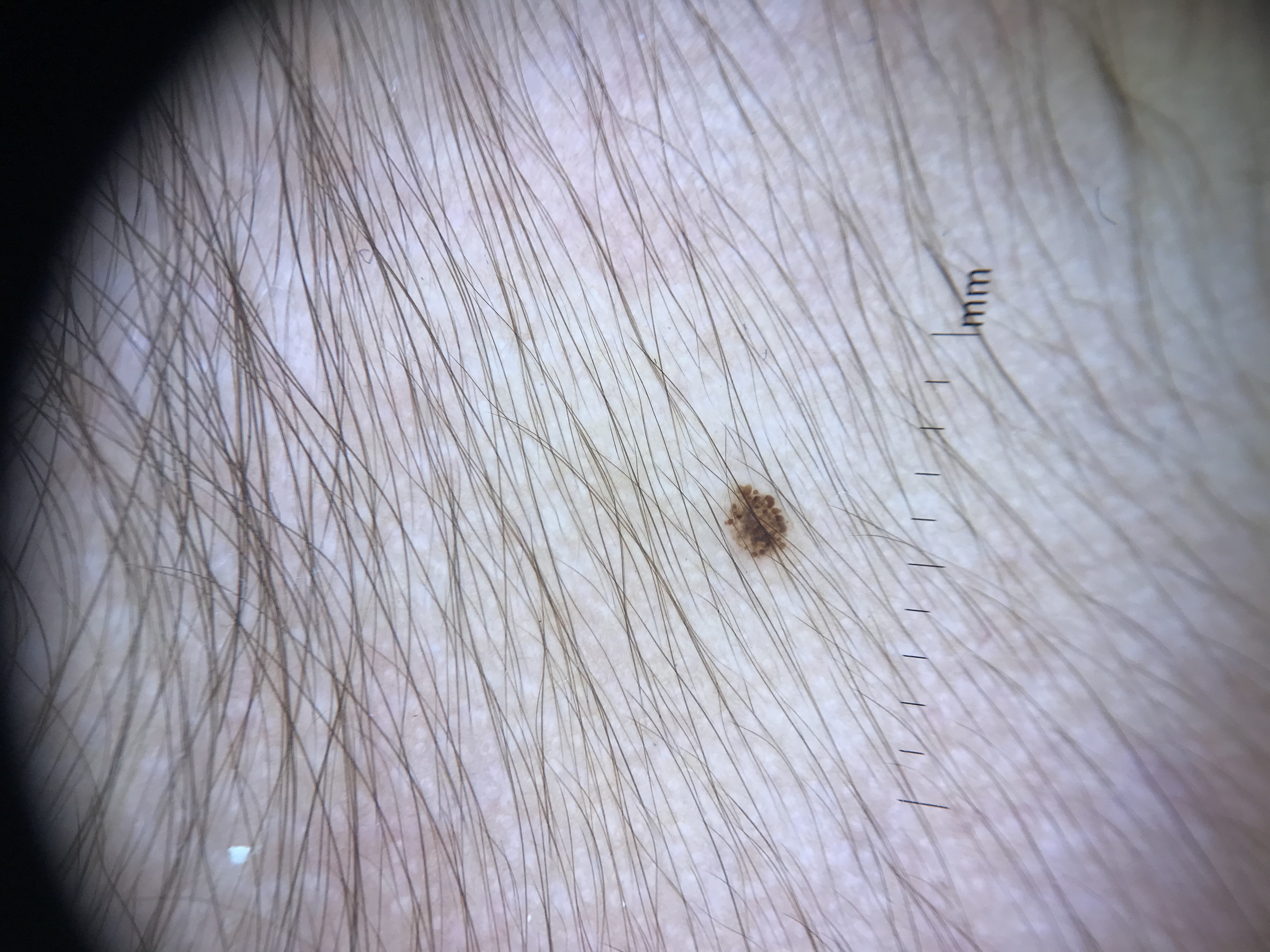Q: What is the imaging modality?
A: dermatoscopy
Q: What is this lesion?
A: dysplastic junctional nevus (expert consensus)